No relevant systemic symptoms · the lesion involves the arm · no relevant lesion symptoms reported · female contributor, age 40–49 · the condition has been present for less than one week · an image taken at a distance · the contributor reports the lesion is rough or flaky — 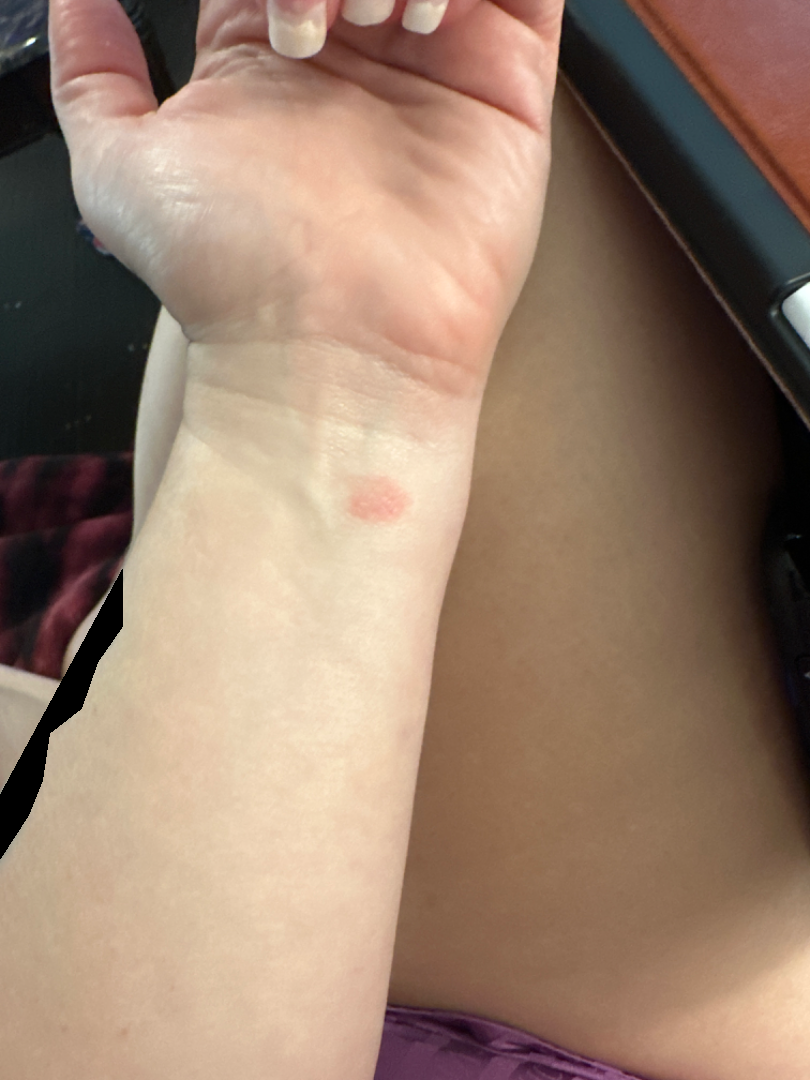| feature | finding |
|---|---|
| differential | Eczema and Allergic Contact Dermatitis were each considered, in no particular order |